The patient described the issue as skin that appeared healthy to them; the photo was captured at an angle; the affected area is the leg and front of the torso; the contributor notes the lesion is raised or bumpy.
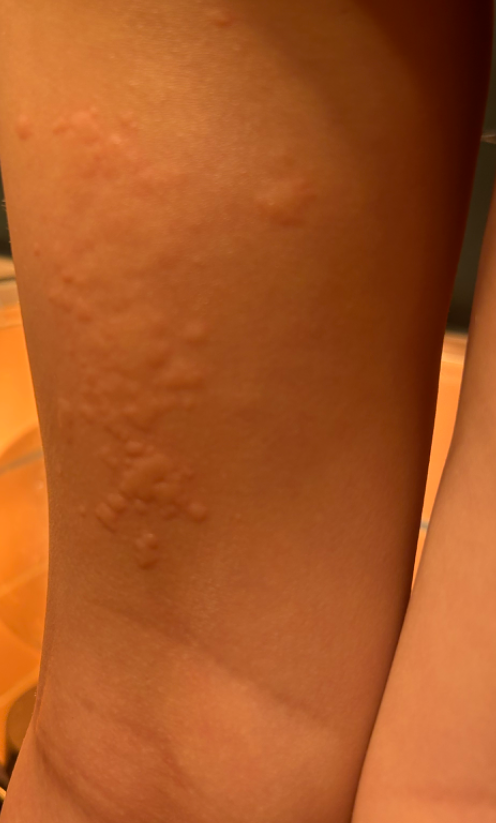differential: Urticaria (favored); Allergic Contact Dermatitis (possible); Insect Bite (less likely)